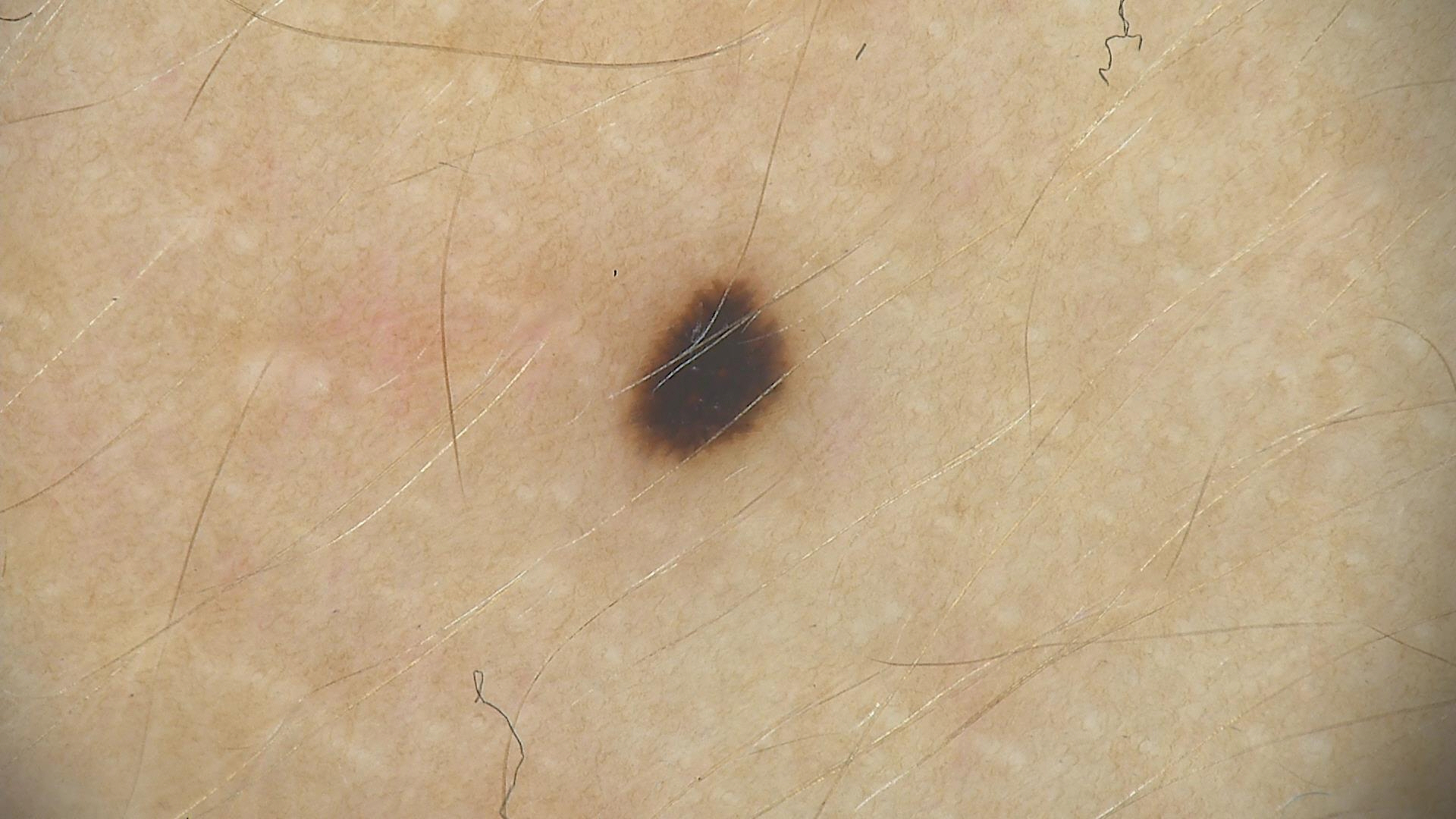Classified as a Spitz/Reed nevus.